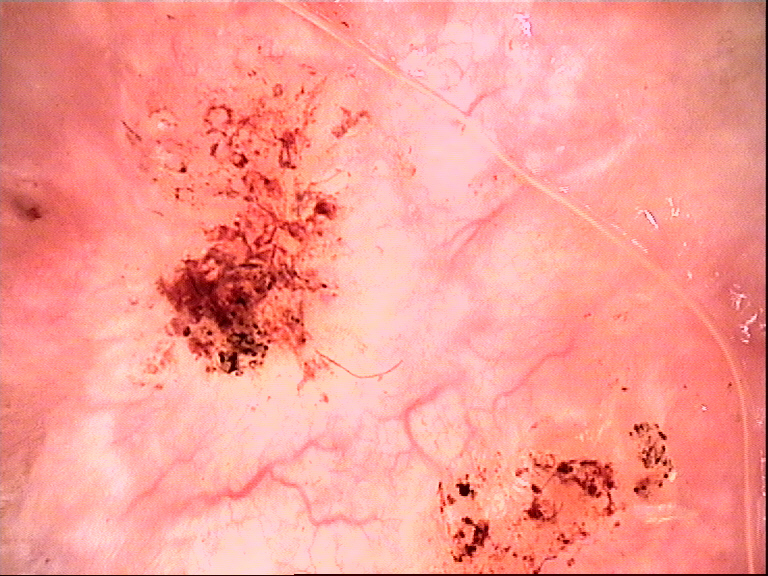Findings:
Dermoscopy of a skin lesion.
Diagnosis:
Histopathologically confirmed as a keratinocytic lesion — a basal cell carcinoma.